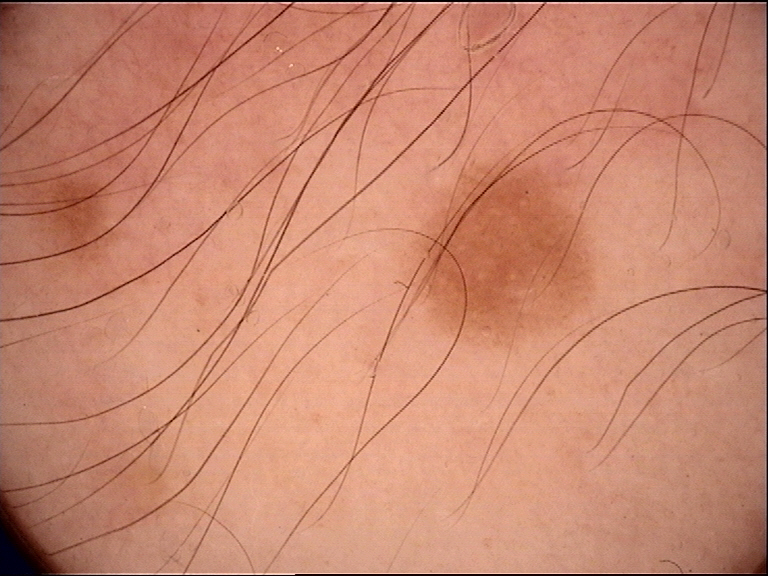Impression: Consistent with a benign lesion — a dysplastic junctional nevus.